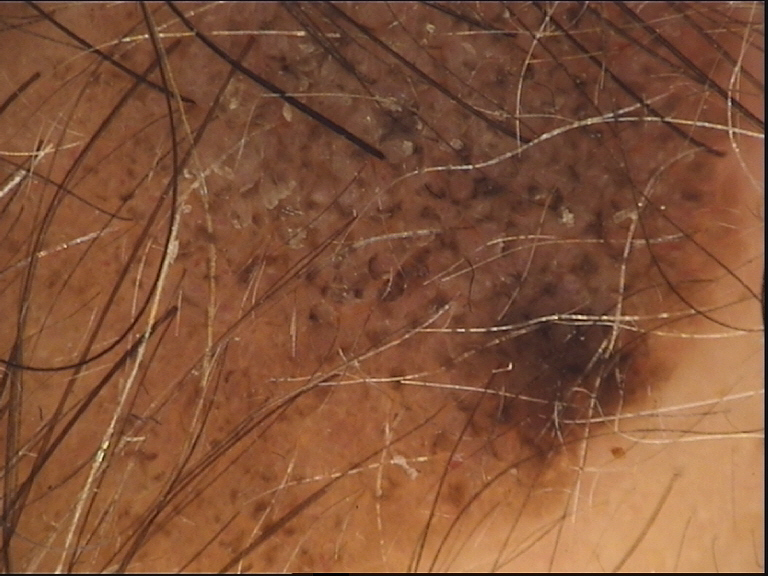A dermoscopic image of a skin lesion. The diagnosis was a banal lesion — a congenital compound nevus.